A female patient 51 years of age; a clinical photograph showing a skin lesion.
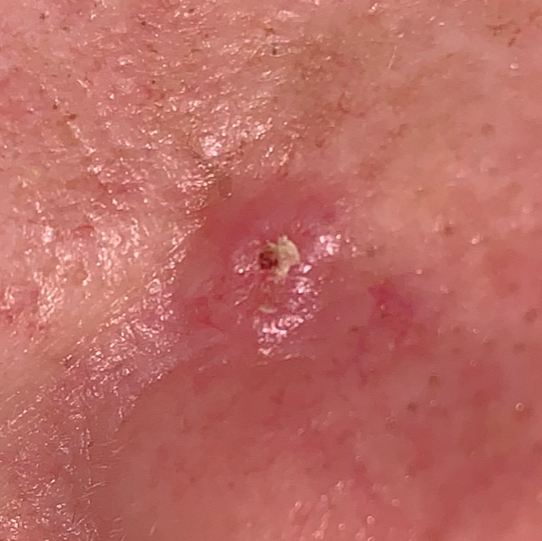Findings:
• region — the nose
• patient-reported symptoms — growth, pain, elevation, bleeding
• pathology — basal cell carcinoma (biopsy-proven)